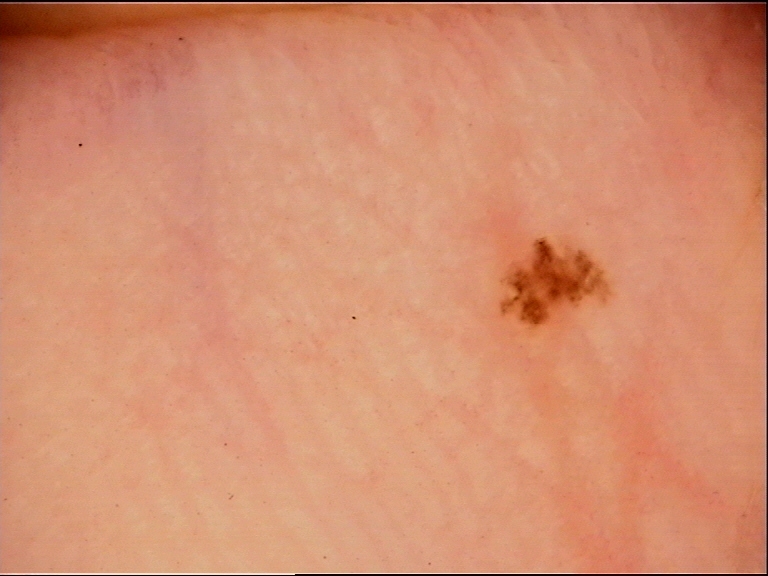A dermoscopic image of a skin lesion.
Consistent with a benign lesion — an acral dysplastic junctional nevus.